A dermoscopic image of a skin lesion:
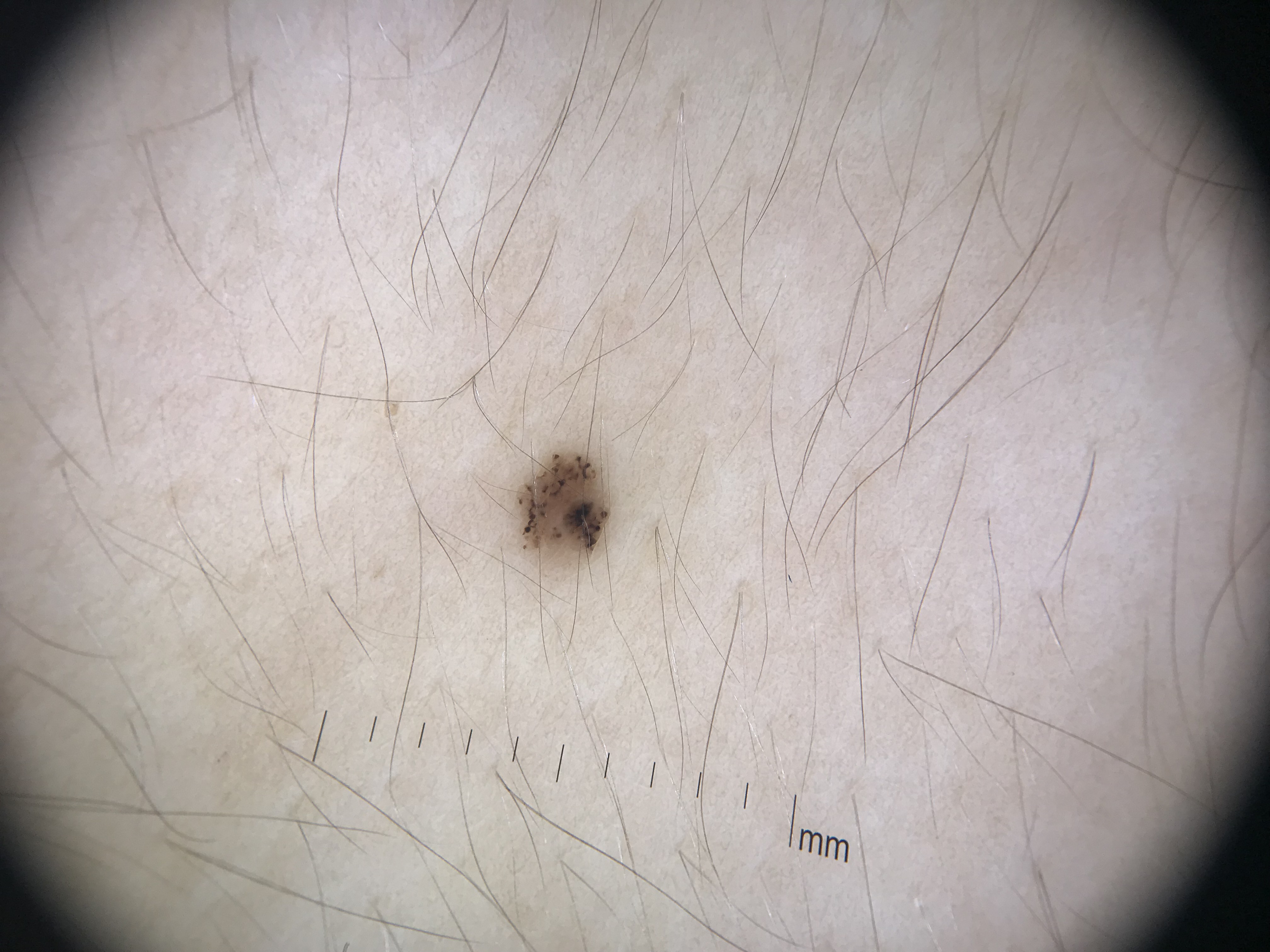Labeled as a dysplastic junctional nevus.